The condition has been present for about one day · the contributor is 40–49, female · the affected area is the leg · the photo was captured at a distance · no associated systemic symptoms reported · no relevant lesion symptoms reported.
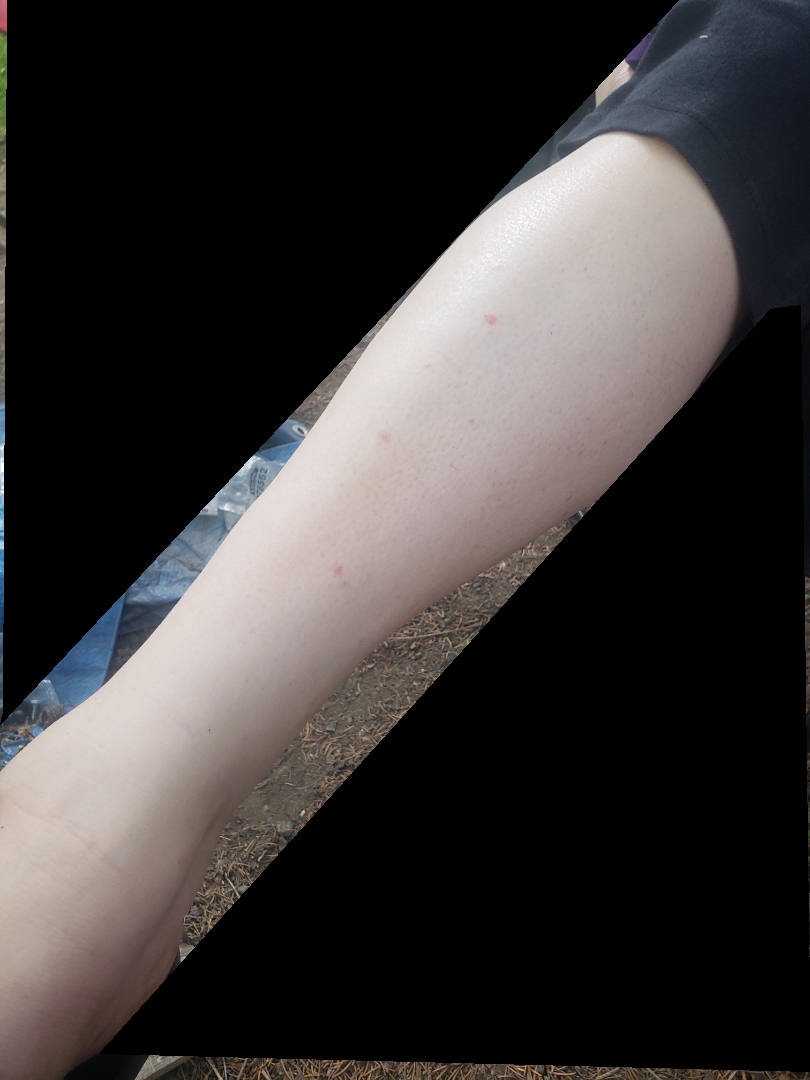The leading consideration is Eczema; also raised was Psoriasis; less probable is Insect Bite.